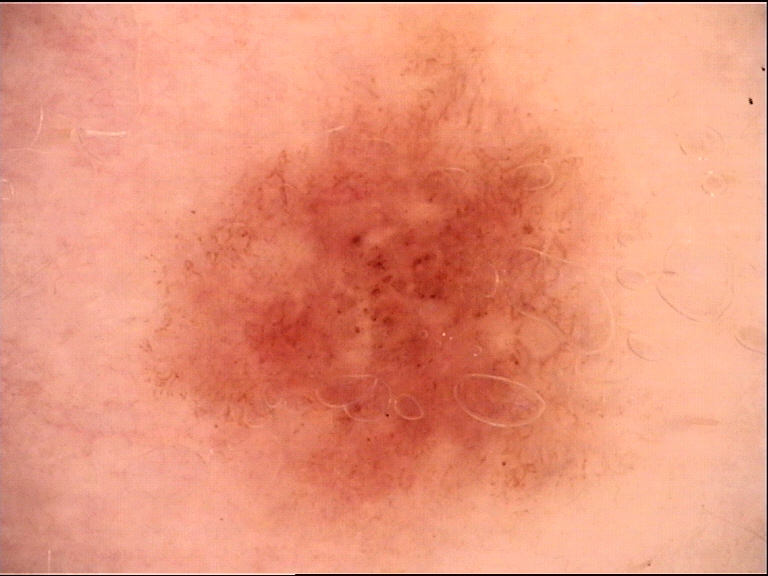• assessment: dysplastic junctional nevus (expert consensus)